Close-up view · the lesion involves the head or neck, leg, back of the hand and arm — 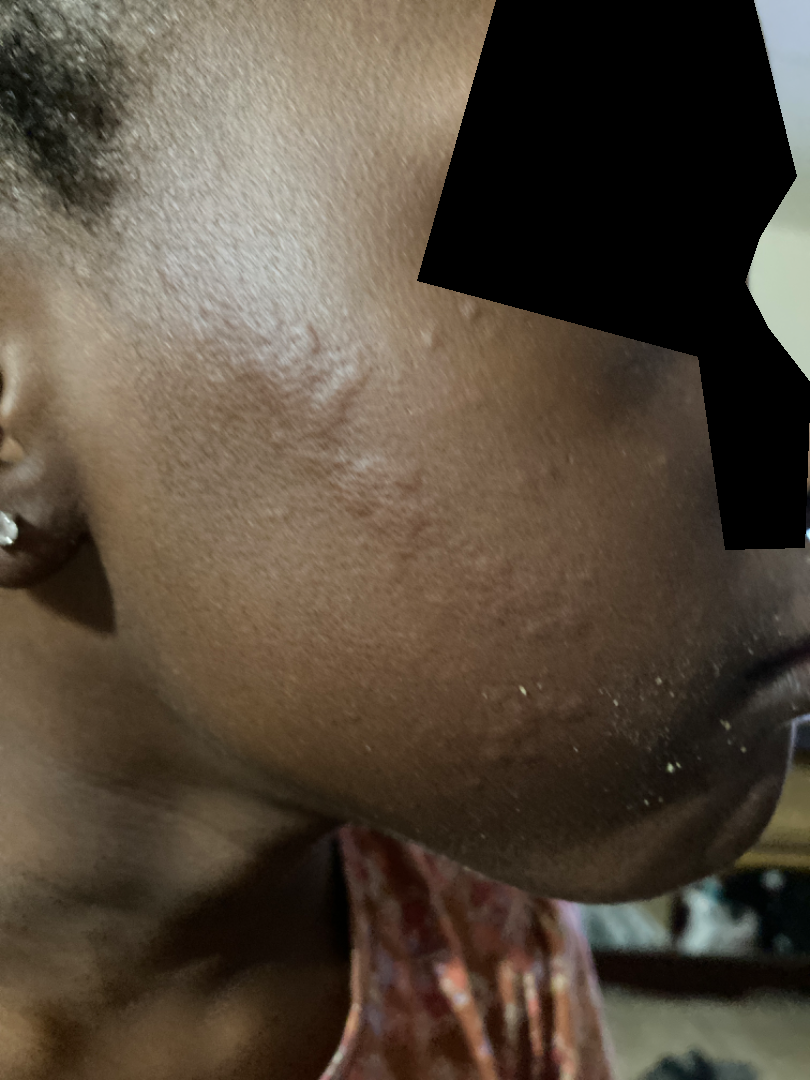The lesion is described as flat. Self-categorized by the patient as a rash. Present for about one day. On photographic review by a dermatologist: the favored diagnosis is Cutaneous sarcoidosis; also consider Cutaneous lupus; less likely is Granuloma faciale.